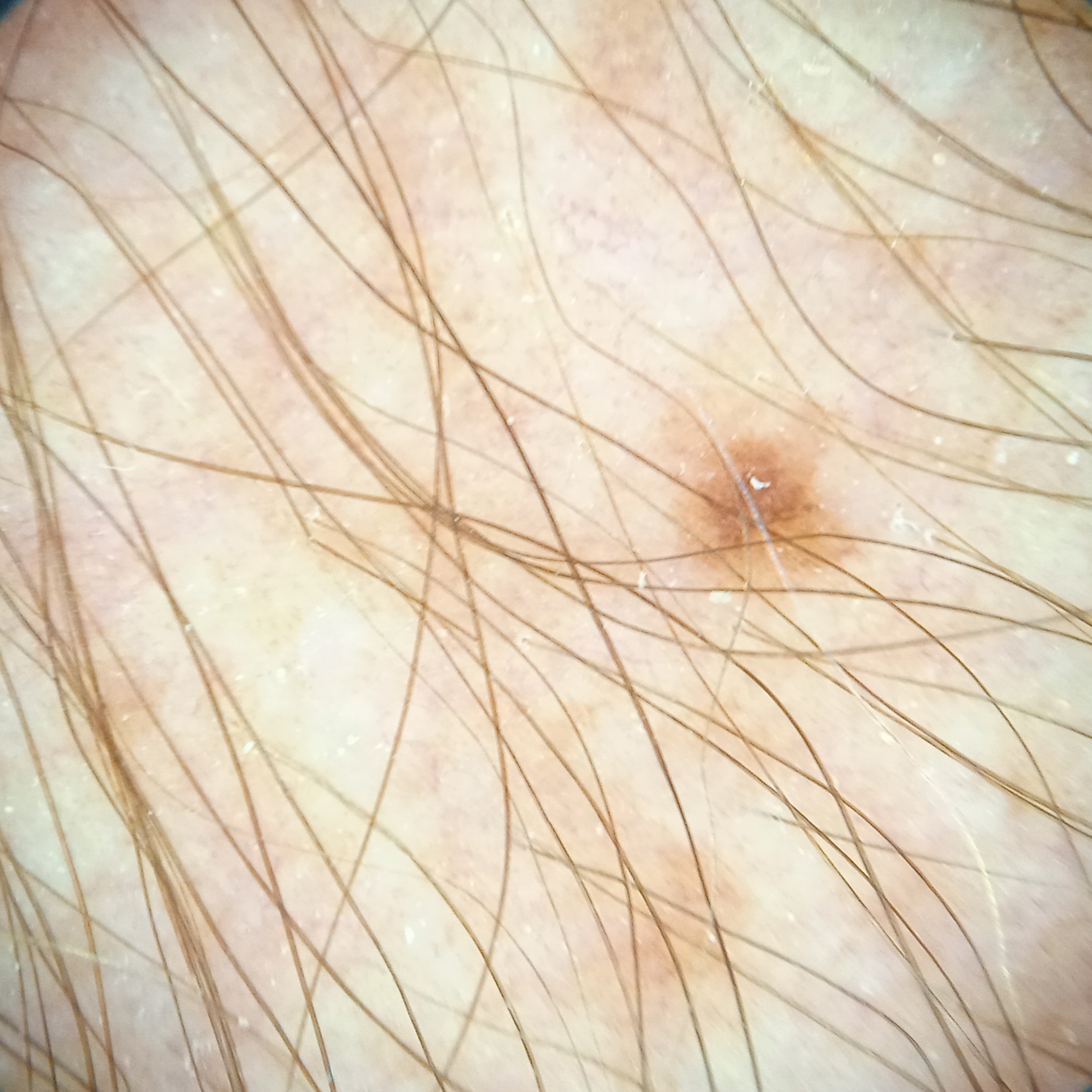sun reaction — skin reddens with sun exposure; patient — male, 76 years old; nevus count — few melanocytic nevi overall; clinical context — research study (no referral diagnosis); location — an arm; size — 8.2 mm; diagnostic label — melanocytic nevus (dermatologist consensus).